A skin lesion imaged with a dermatoscope.
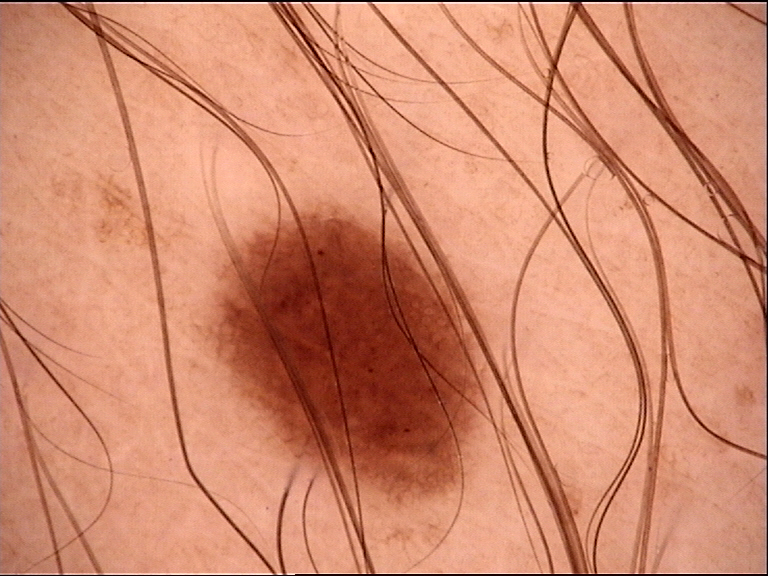Labeled as a dysplastic junctional nevus.